Dermoscopy of a skin lesion.
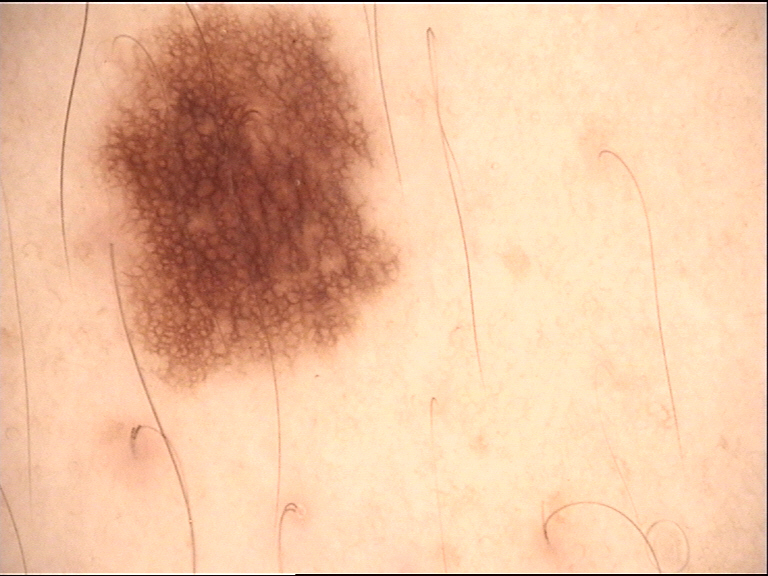Consistent with a banal lesion — a junctional nevus.